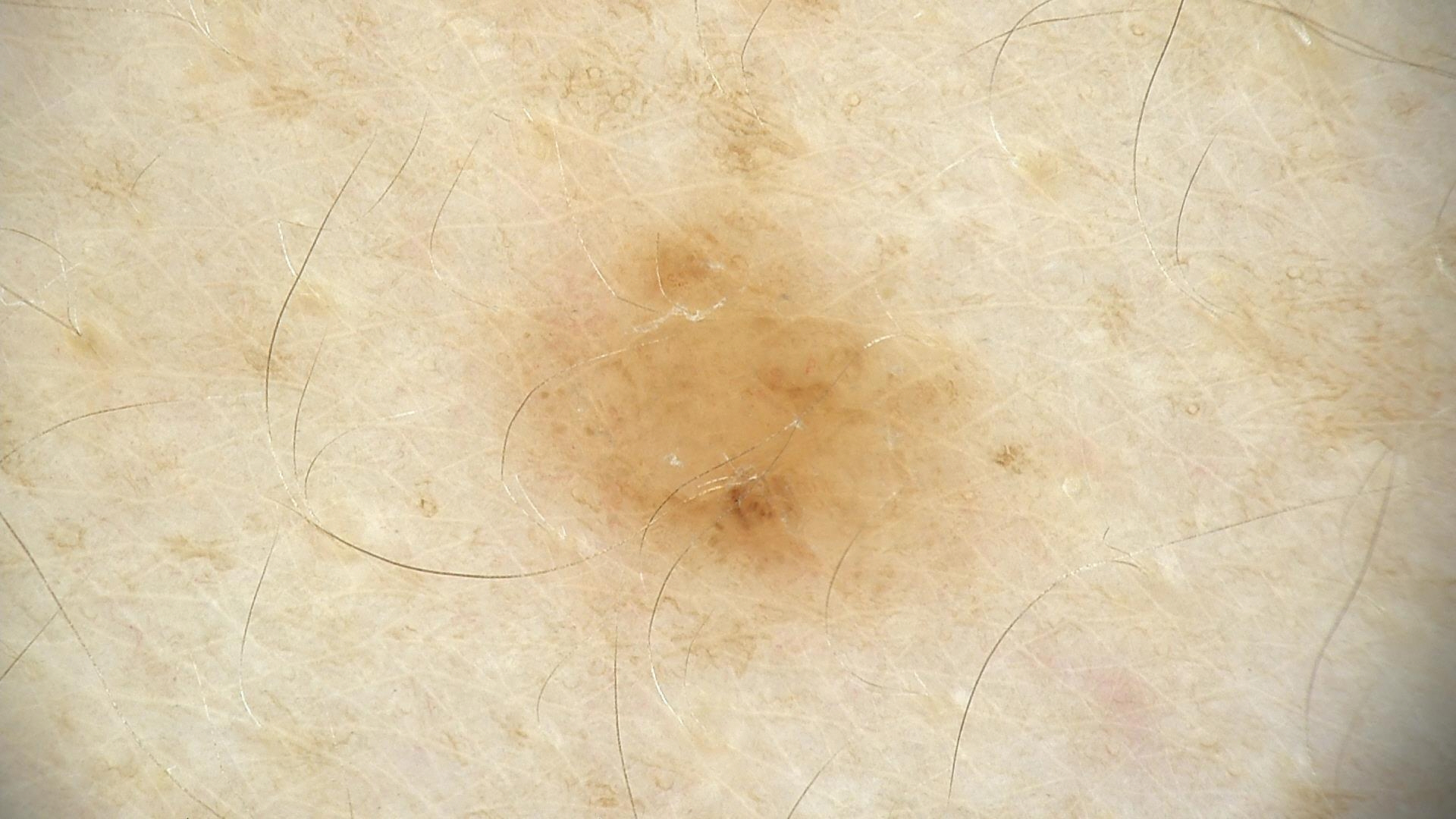Case:
A dermoscopy image of a single skin lesion.
Impression:
Classified as a benign lesion — a dysplastic junctional nevus.